The lesion involves the back of the hand and arm · an image taken at an angle · the lesion is described as raised or bumpy · the contributor notes the condition has been present for one to four weeks: 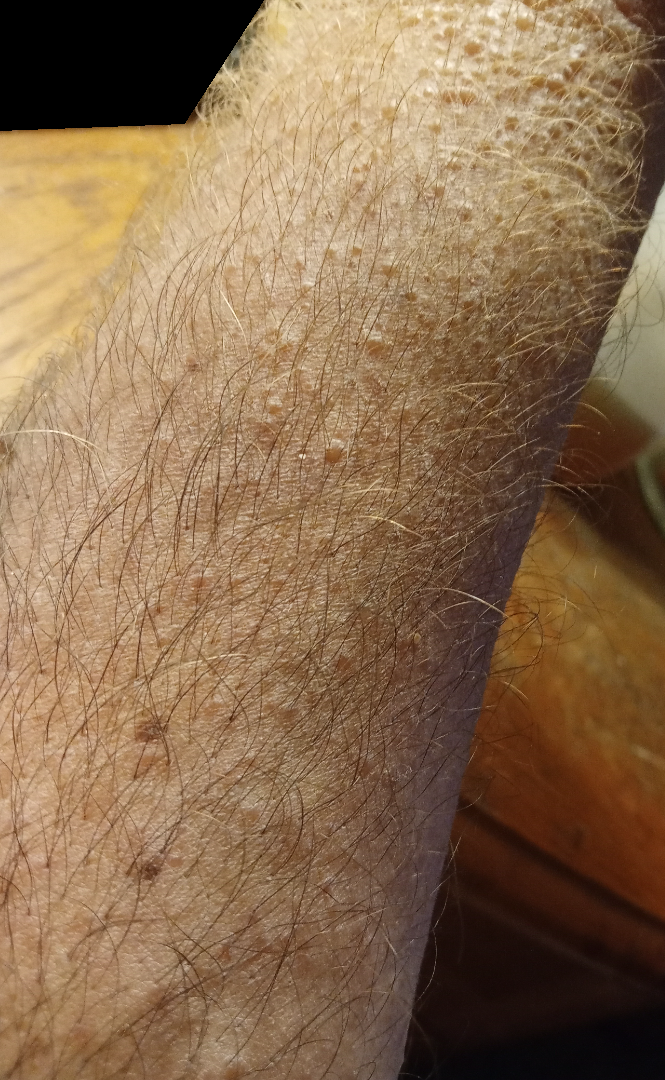Q: What is the differential diagnosis?
A: Impetigo, Lichen Simplex Chronicus and Allergic Contact Dermatitis were considered with similar weight